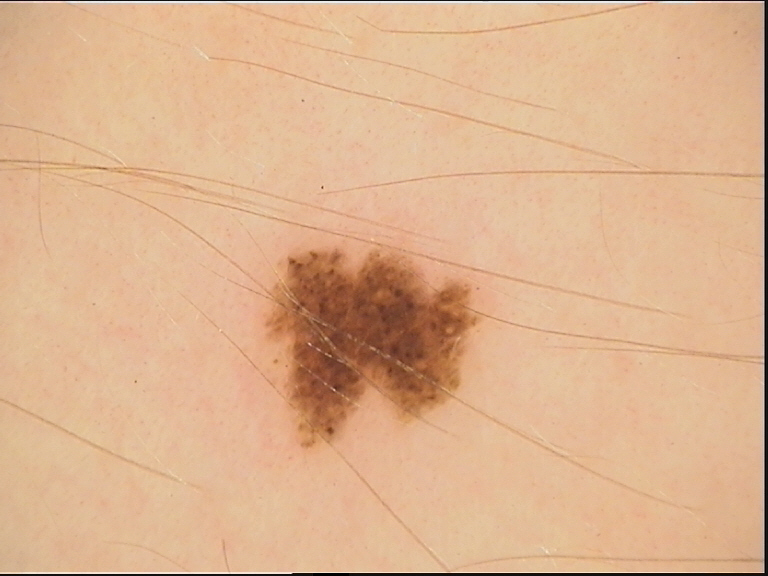- class: dysplastic junctional nevus (expert consensus)